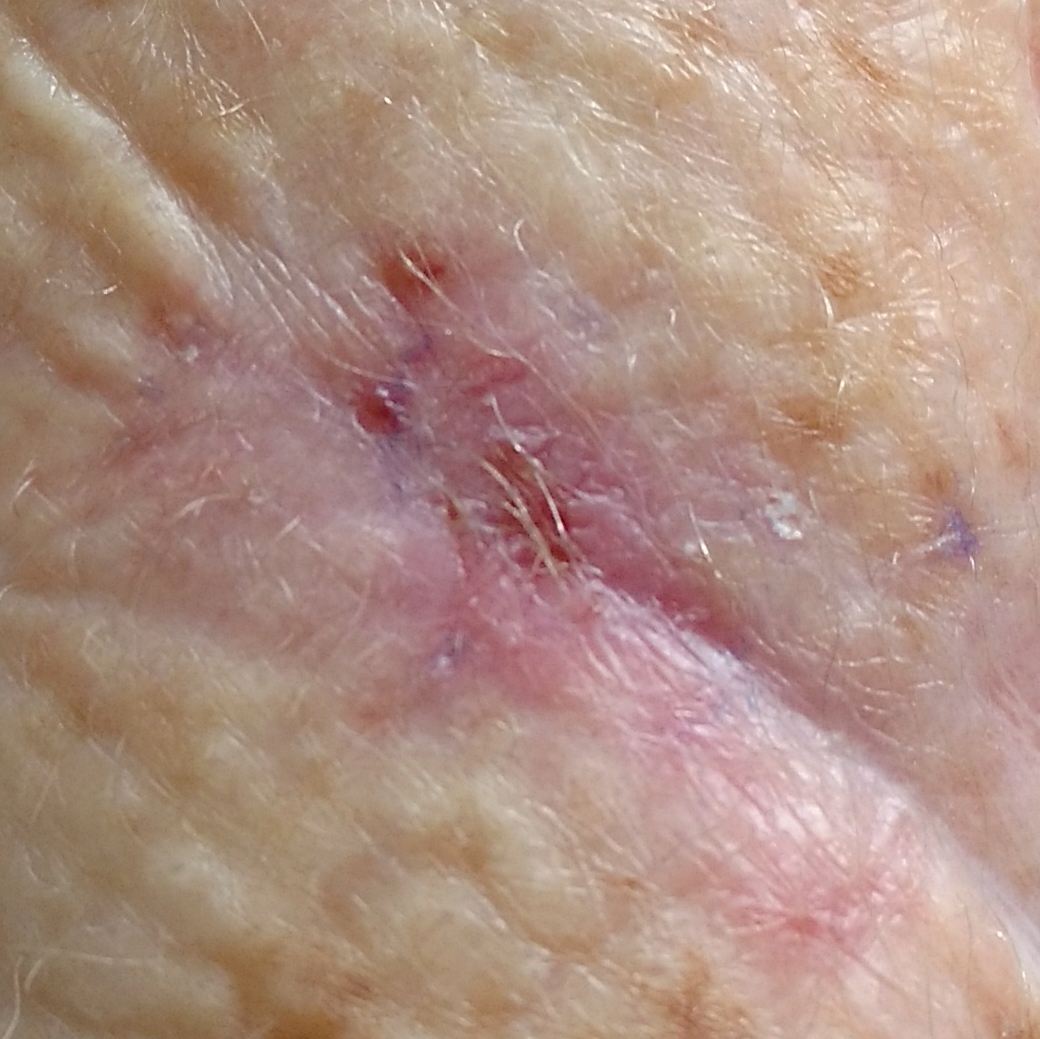{
  "diagnosis": {
    "name": "basal cell carcinoma",
    "code": "BCC",
    "malignancy": "malignant",
    "confirmation": "histopathology"
  }
}